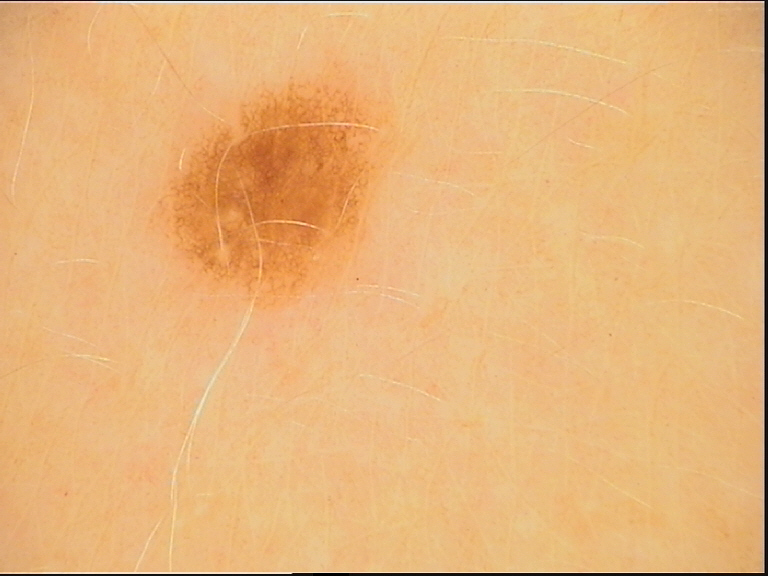Q: What kind of image is this?
A: dermoscopy
Q: What is this lesion?
A: dysplastic junctional nevus (expert consensus)